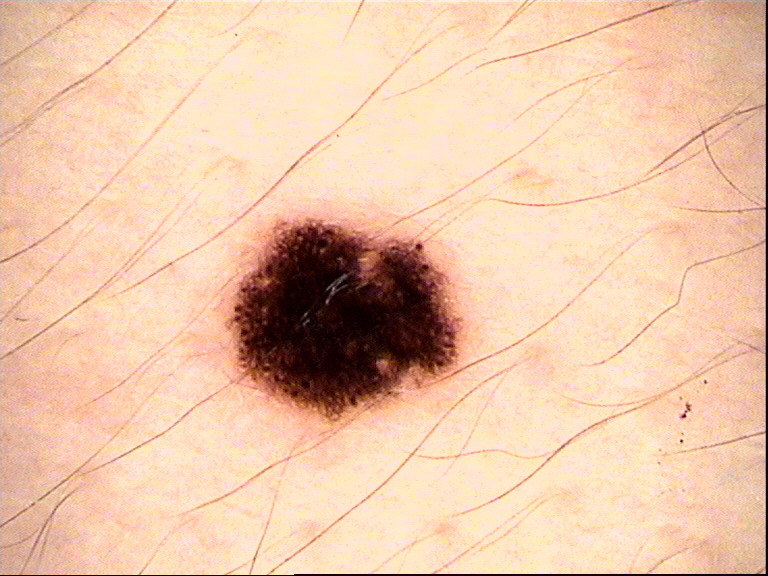A skin lesion imaged with a dermatoscope. Classified as a dysplastic junctional nevus.